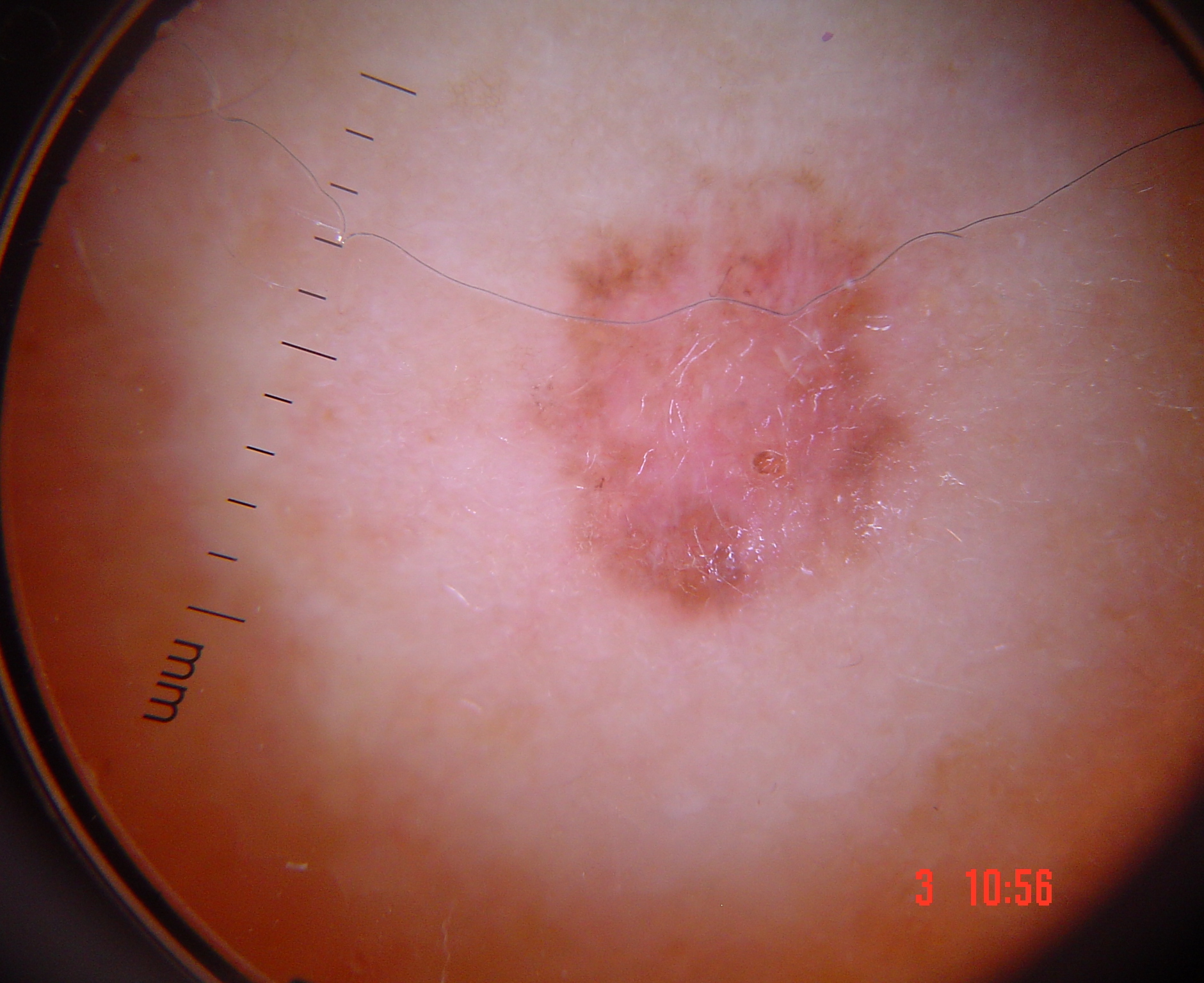<case>
  <diagnosis>
    <name>basal cell carcinoma</name>
    <code>bcc</code>
    <malignancy>malignant</malignancy>
    <super_class>non-melanocytic</super_class>
    <confirmation>histopathology</confirmation>
  </diagnosis>
</case>